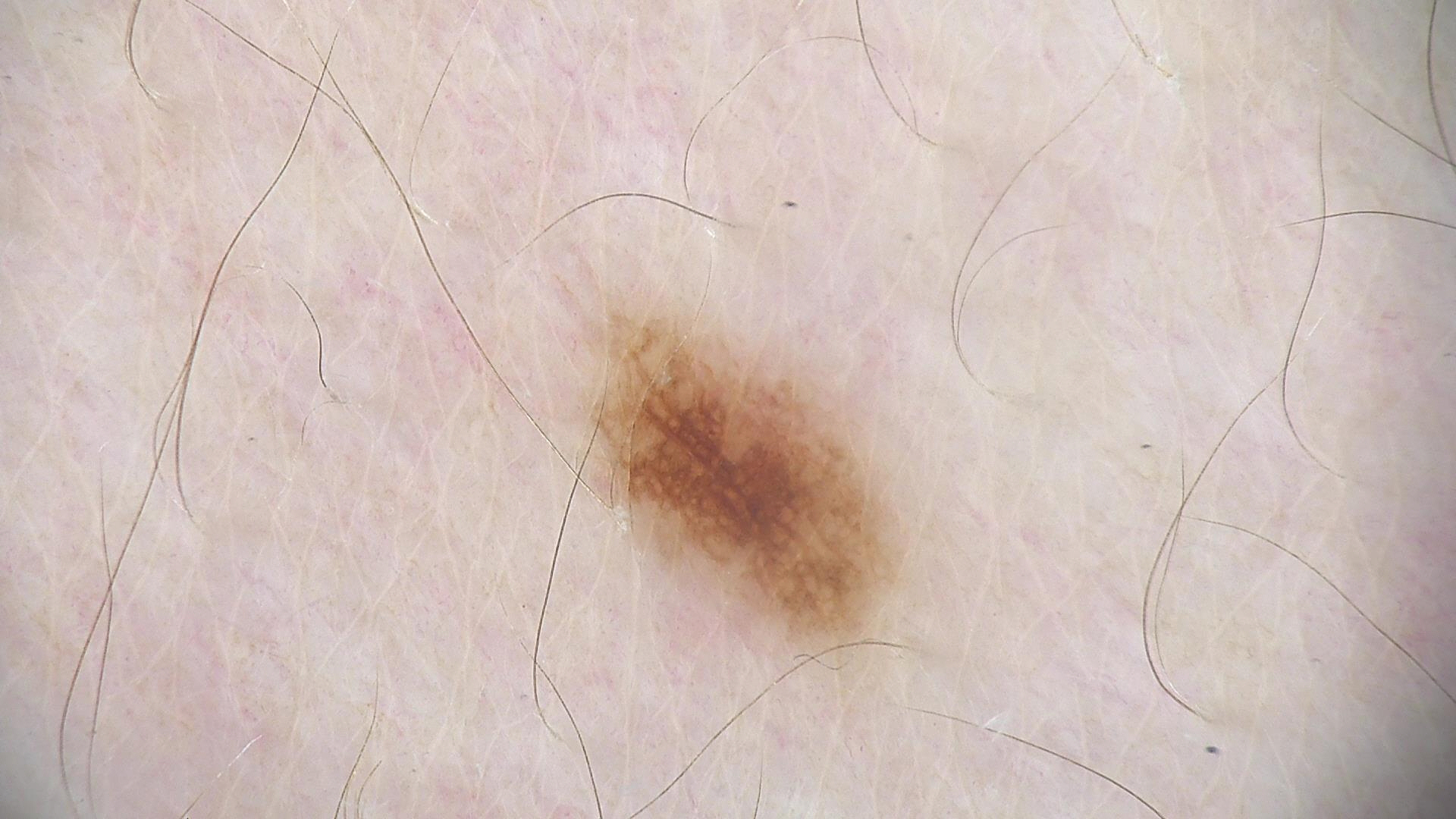Q: What is the diagnosis?
A: dysplastic junctional nevus (expert consensus)